No constitutional symptoms were reported. Located on the front of the torso. Texture is reported as flat. The patient is 60–69, female. The patient described the issue as a rash. No relevant lesion symptoms reported. The photo was captured at a distance.
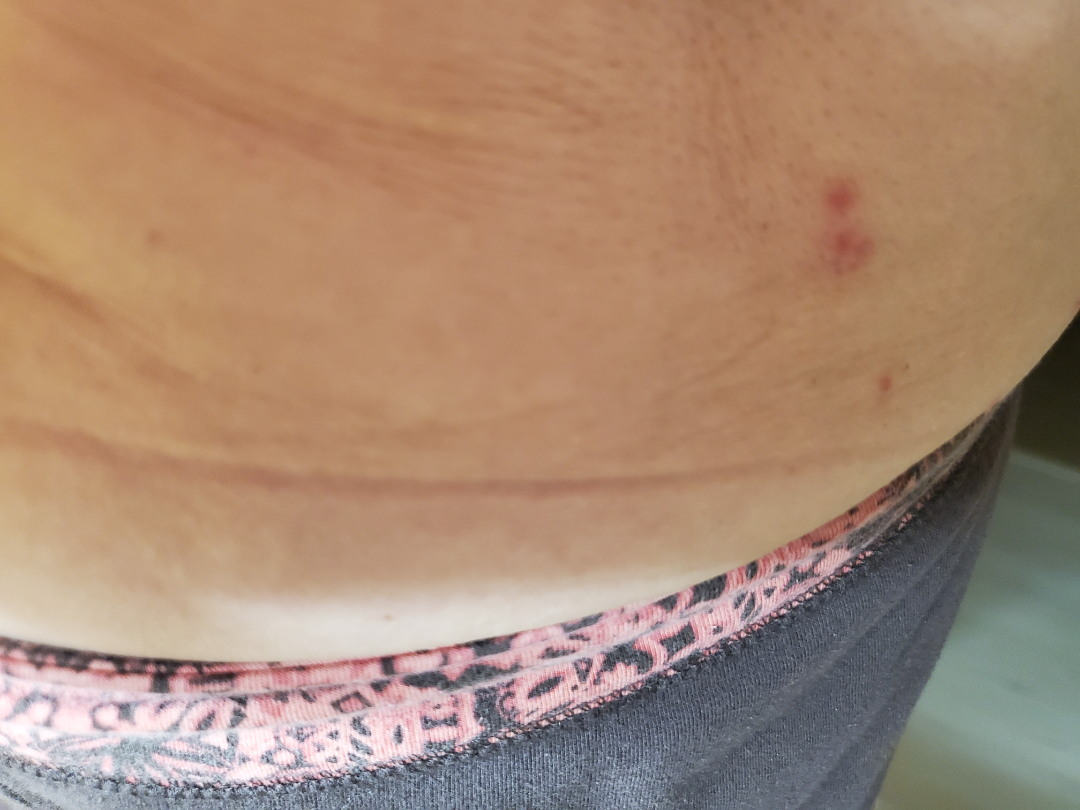Impression: The case was difficult to assess from the available photograph.